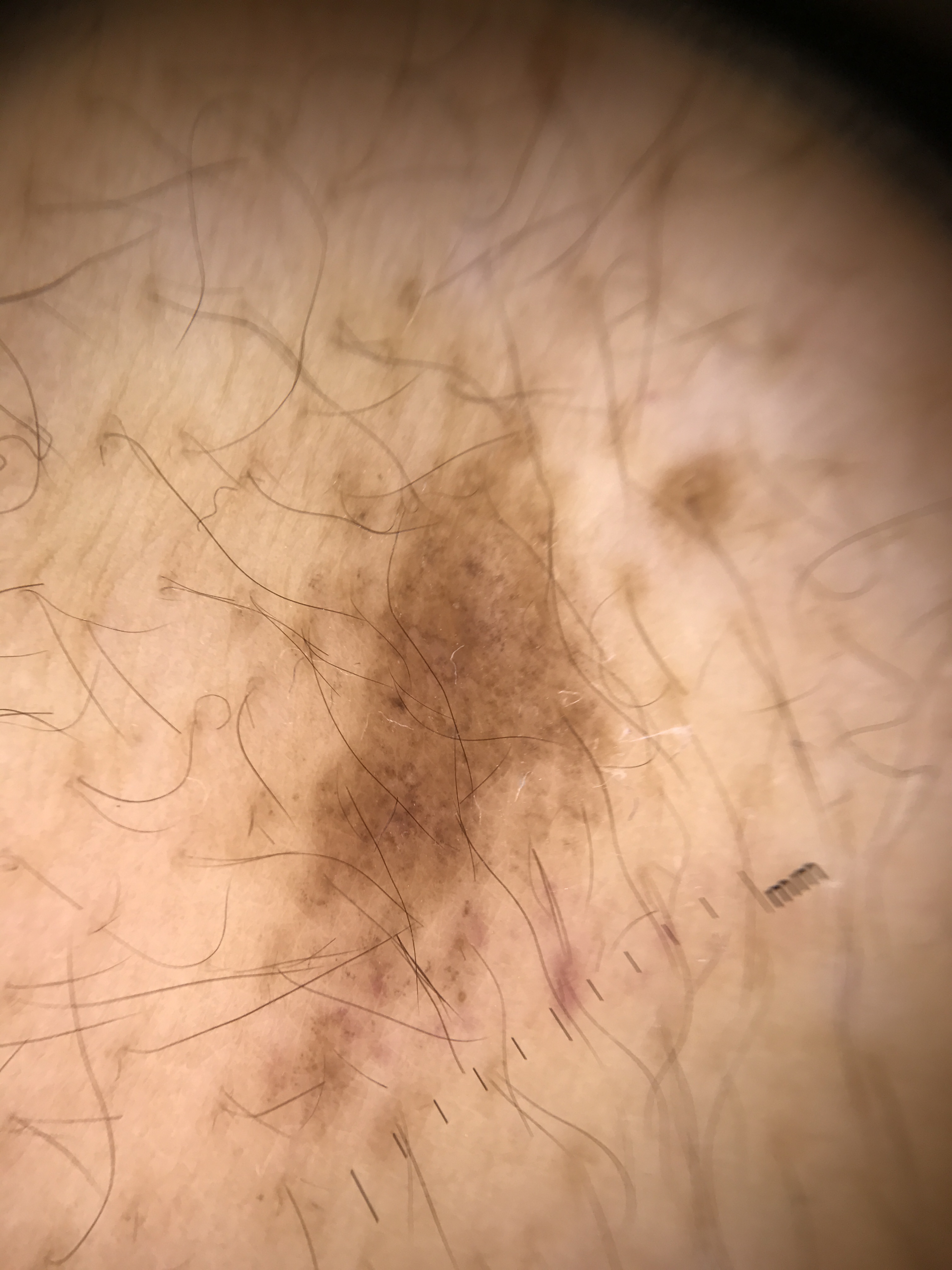A dermatoscopic image of a skin lesion.
The diagnosis was a congenital junctional nevus.